The affected area is the front of the torso and arm · this is a close-up image: 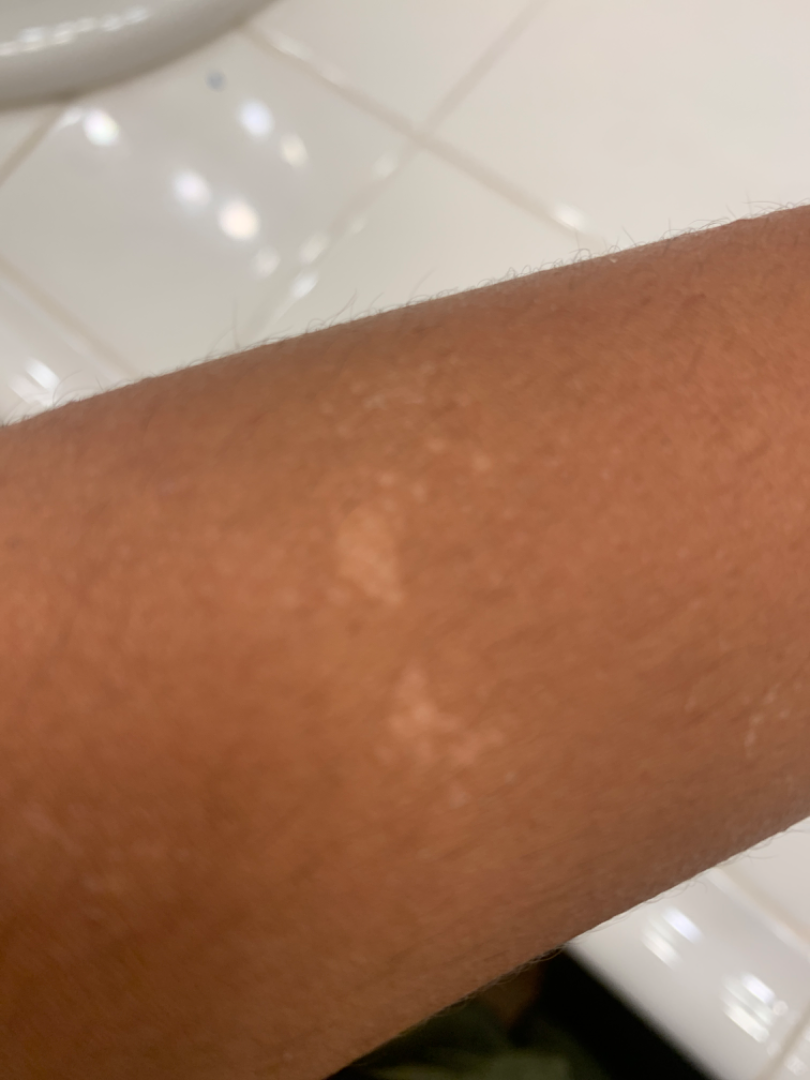assessment: could not be assessed, self-categorized as: a pigmentary problem, described texture: rough or flaky.